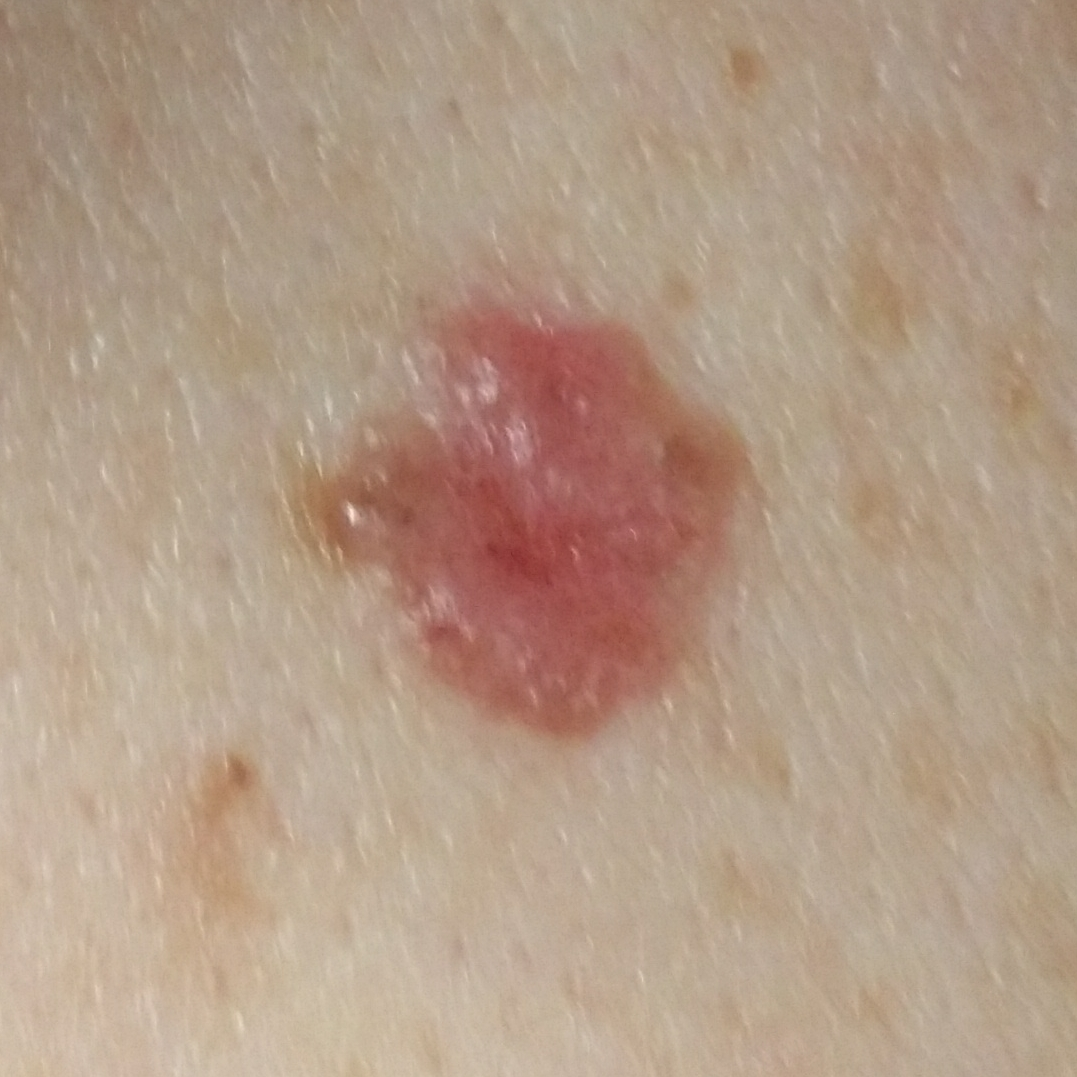  risk_factors:
    positive:
      - prior skin cancer (patient or family)
    negative:
      - pesticide exposure
  symptoms:
    present:
      - elevation
  diagnosis:
    name: basal cell carcinoma
    code: BCC
    malignancy: malignant
    confirmation: histopathology